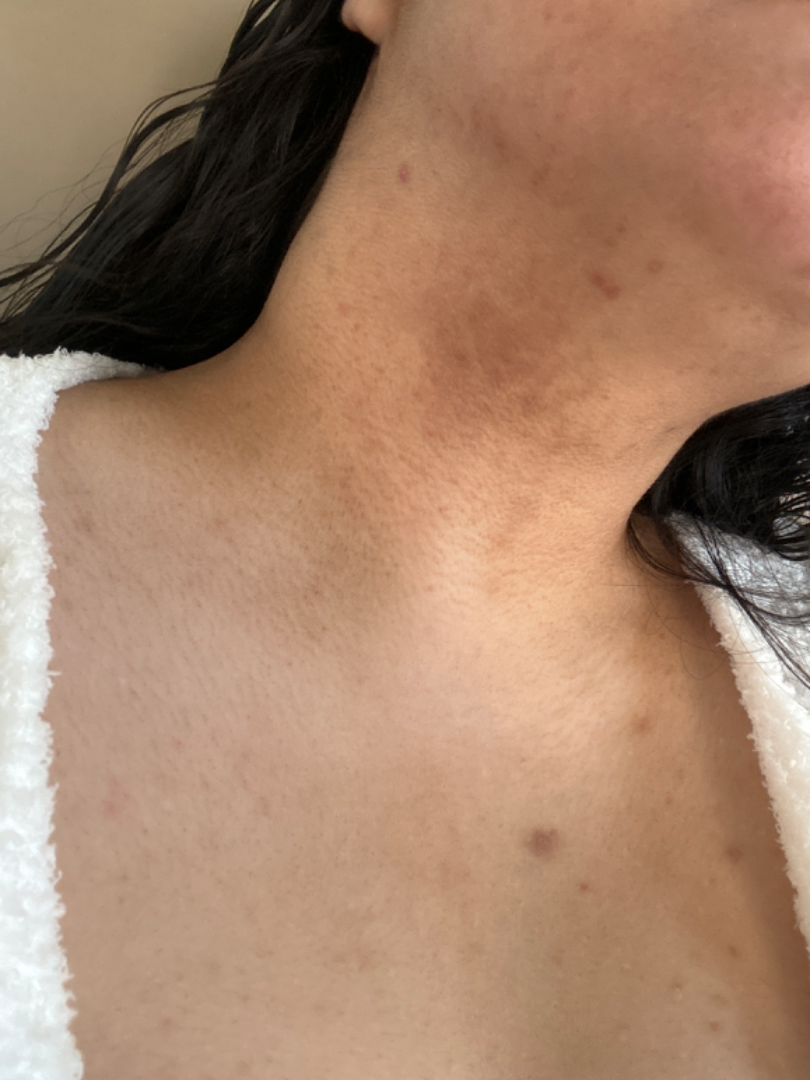Clinical context: The photograph was taken at an angle. Reported duration is one to three months. Texture is reported as rough or flaky. The patient is 18–29, female. The lesion is associated with darkening and bothersome appearance. The affected area is the head or neck. The patient described the issue as acne. Assessment: The reviewing dermatologist's impression was: Erythema dyschromicum perstans (primary); Post-Inflammatory hyperpigmentation (considered).